A dermoscopic close-up of a skin lesion.
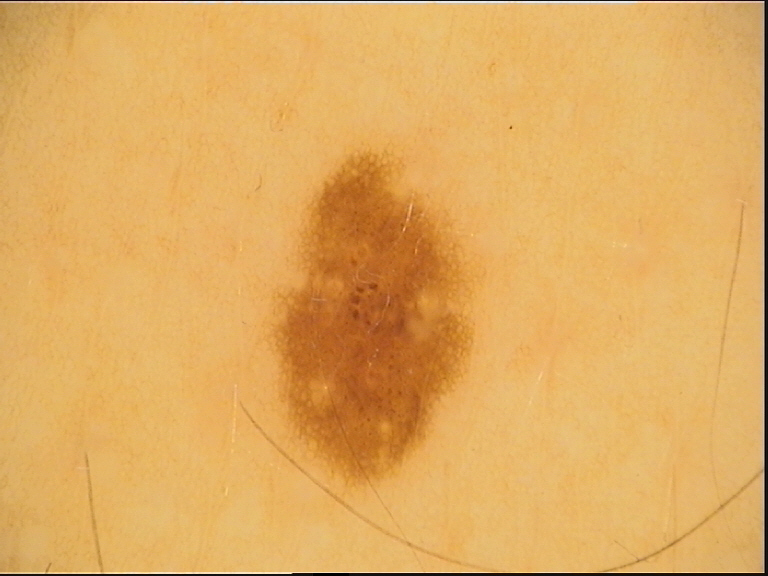diagnostic label: dysplastic junctional nevus (expert consensus).